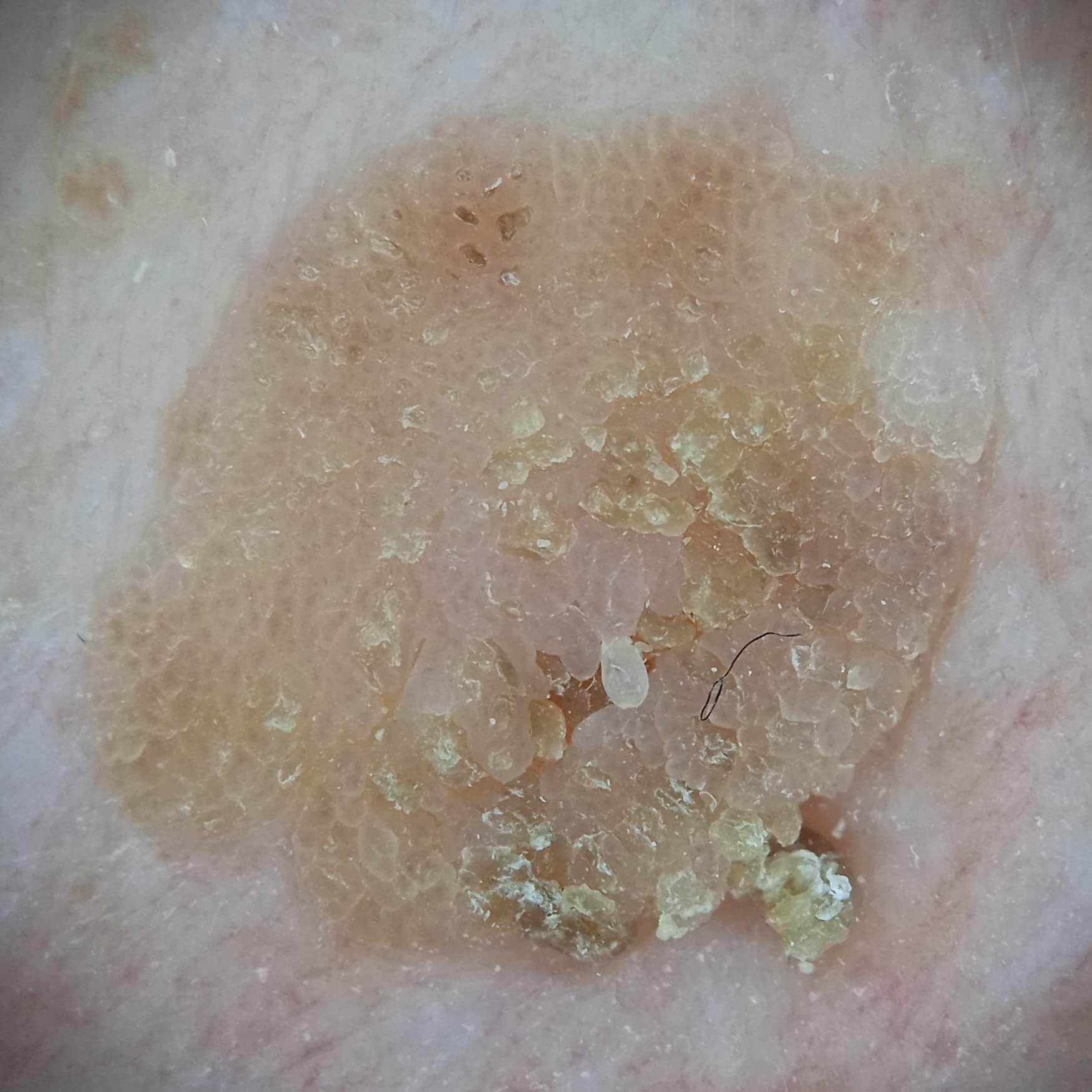{
  "referral": "research study (no referral diagnosis)",
  "patient": {
    "age": 62,
    "sex": "male"
  },
  "image": "dermatoscopic image",
  "lesion_size": {
    "diameter_mm": 11.3
  },
  "diagnosis": {
    "name": "seborrheic keratosis",
    "malignancy": "benign"
  }
}